Close-up view: 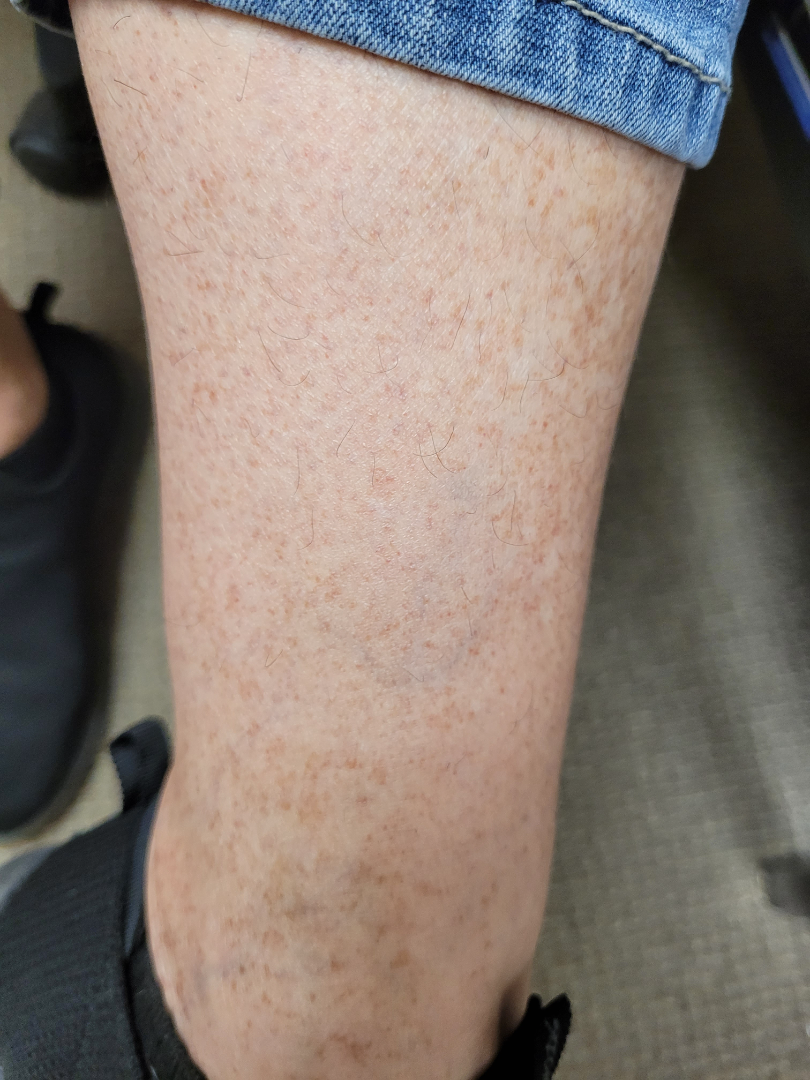One reviewing dermatologist: the primary impression is Pigmented purpuric eruption; an alternative is Stasis Dermatitis; with consideration of Hemosiderin pigmentation of skin.